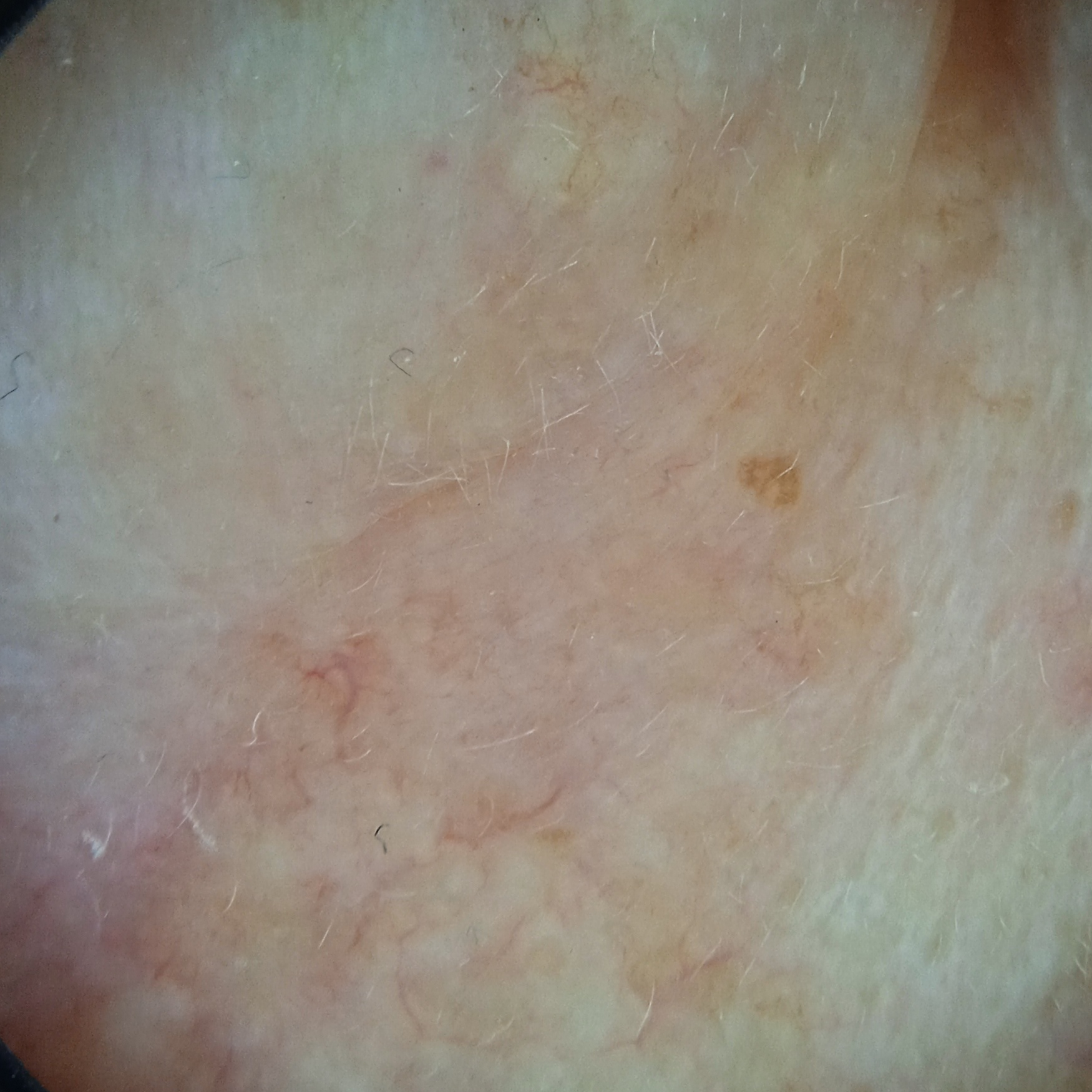Clinical context:
A dermatoscopic image of a skin lesion. The patient says their skin tans without first burning. A female patient 68 years of age. The patient describes having few moles overall. The lesion is on the face.
Impression:
The lesion was assessed as a basal cell carcinoma.